A male subject 61 years old · a clinical photo of a skin lesion taken with a smartphone · Fitzpatrick II: 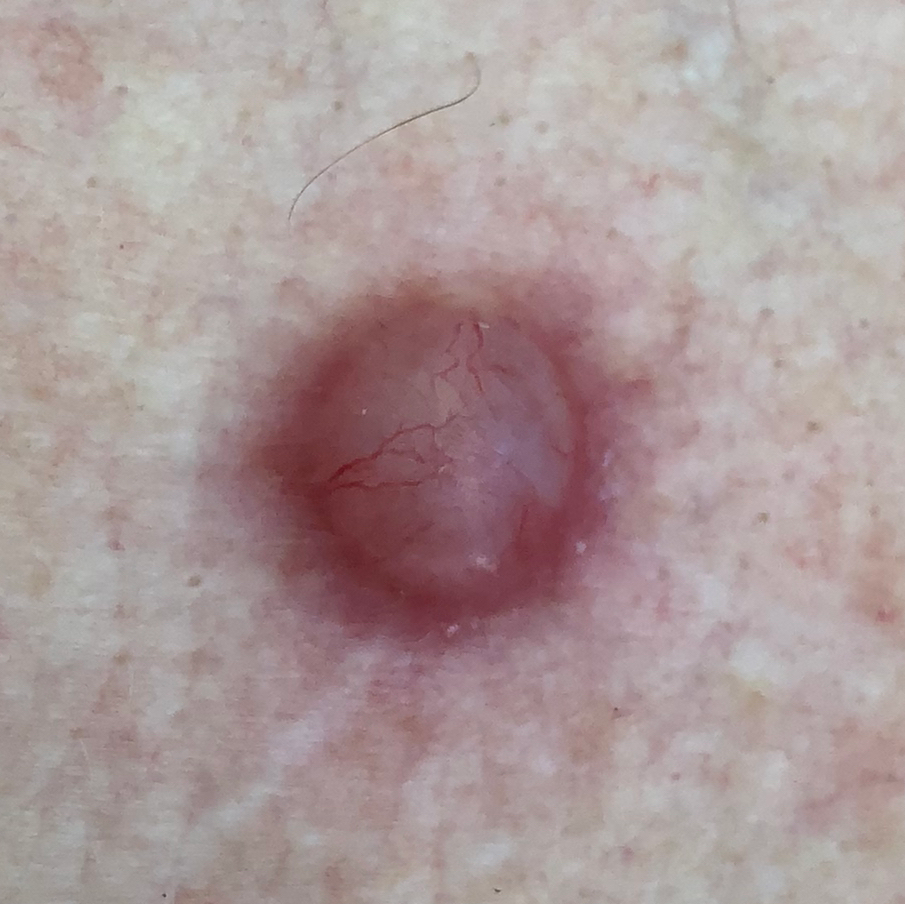| feature | finding |
|---|---|
| site | the chest |
| lesion size | 10 × 10 mm |
| diagnostic label | basal cell carcinoma (biopsy-proven) |